A skin lesion imaged with a dermatoscope.
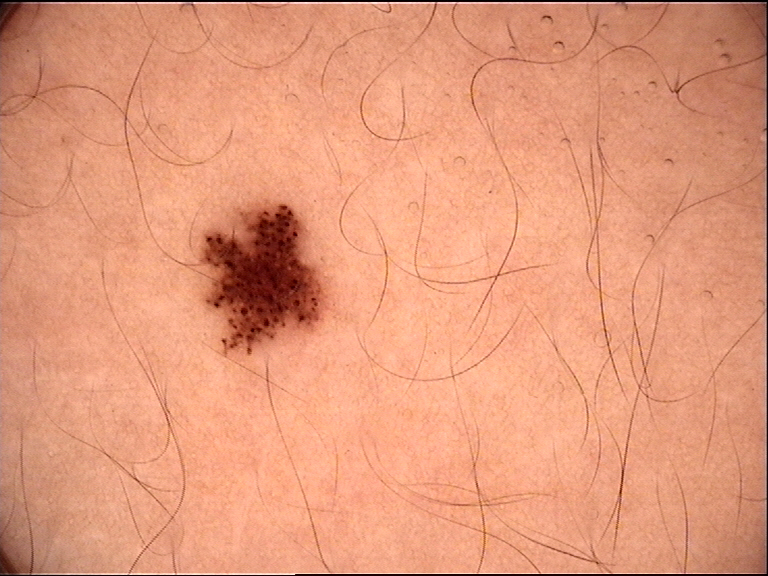Classified as a compound nevus.